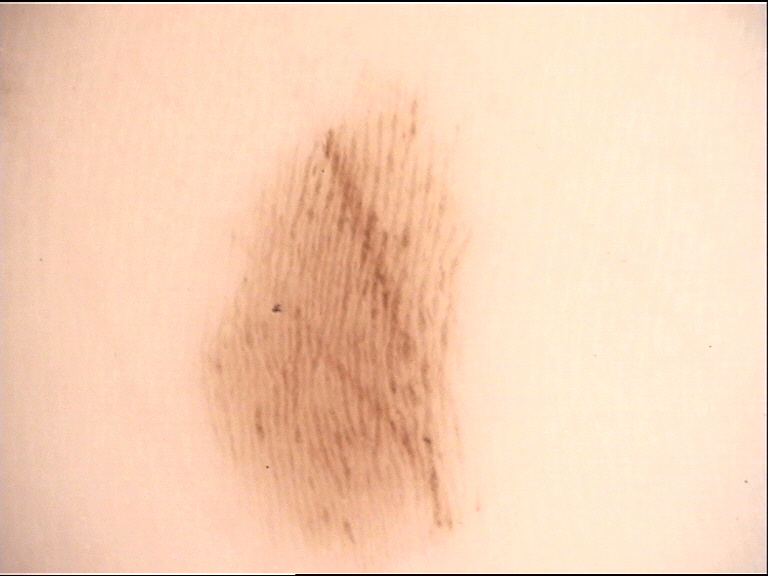A dermoscopic close-up of a skin lesion. Diagnosed as a banal lesion — an acral junctional nevus.